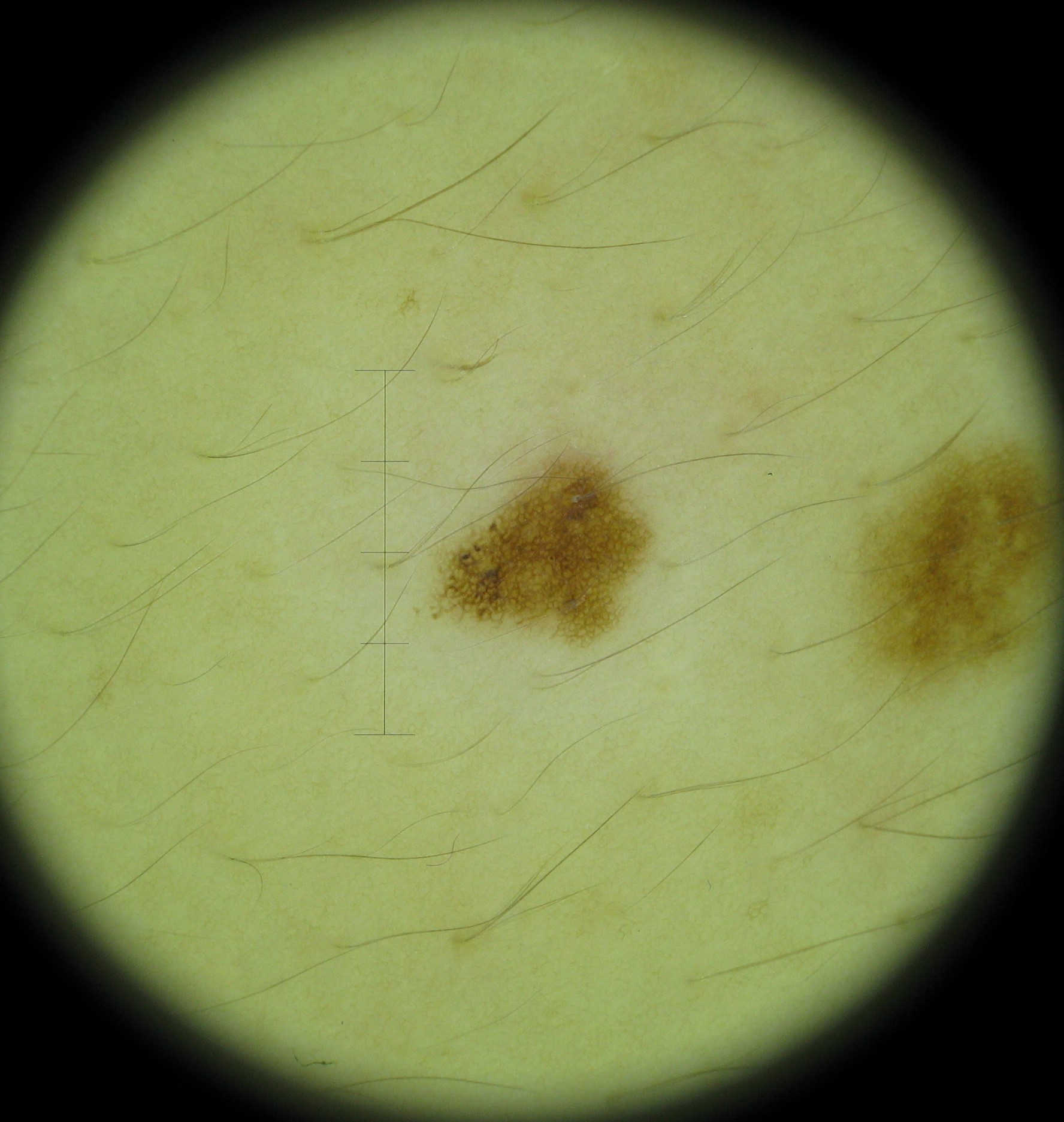{"diagnosis": {"name": "dysplastic junctional nevus", "code": "jd", "malignancy": "benign", "super_class": "melanocytic", "confirmation": "expert consensus"}}